A dermoscopic close-up of a skin lesion.
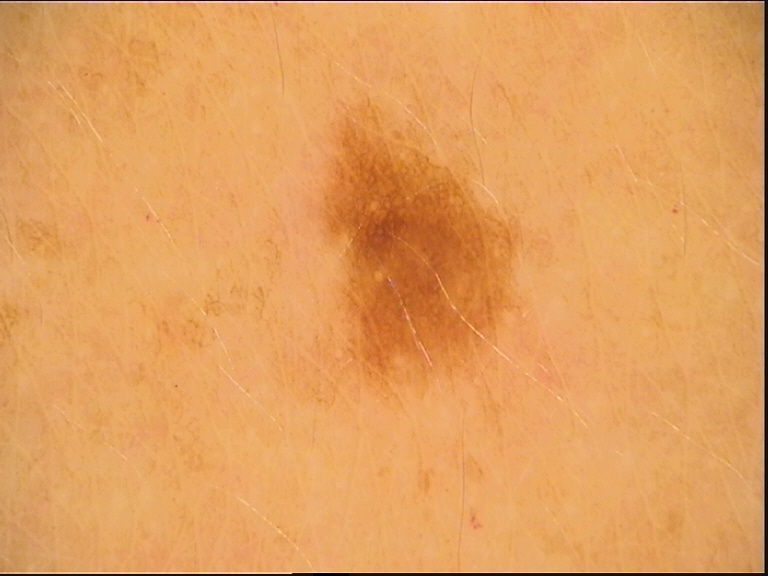category: banal
diagnosis: junctional nevus (expert consensus)